A close-up photograph: 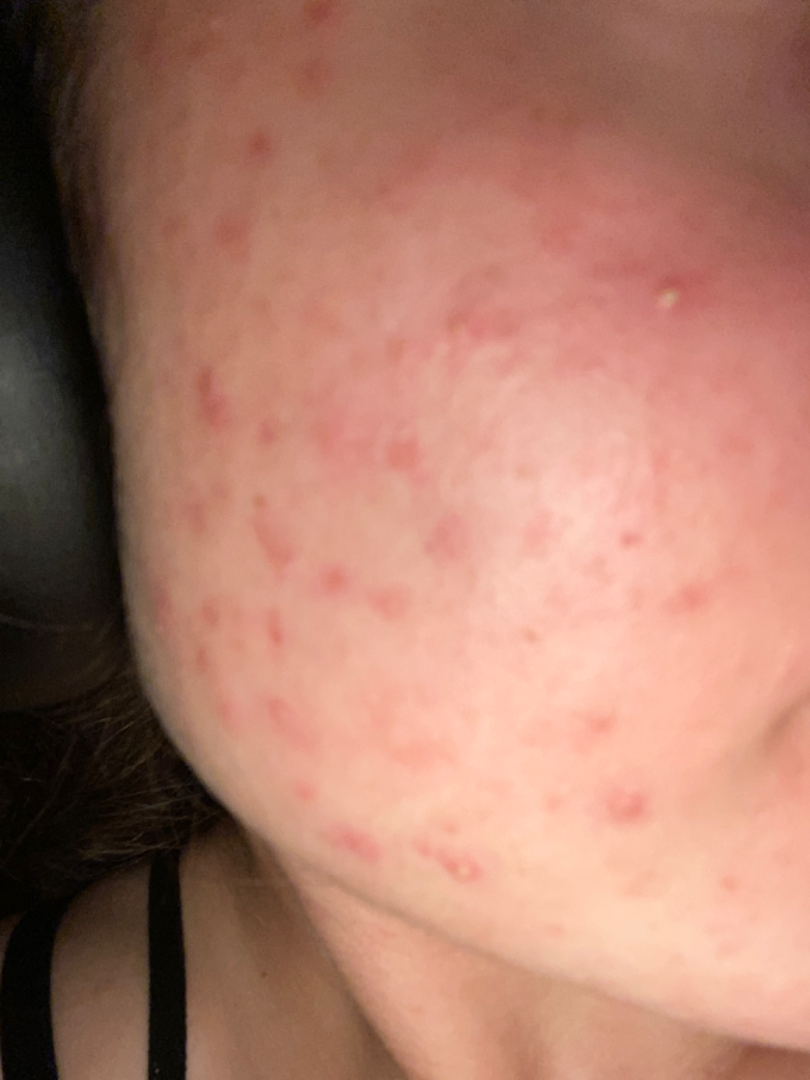Findings: The impression is Acne.